A clinical photograph showing a skin lesion in context; a female subject approximately 85 years of age or older: 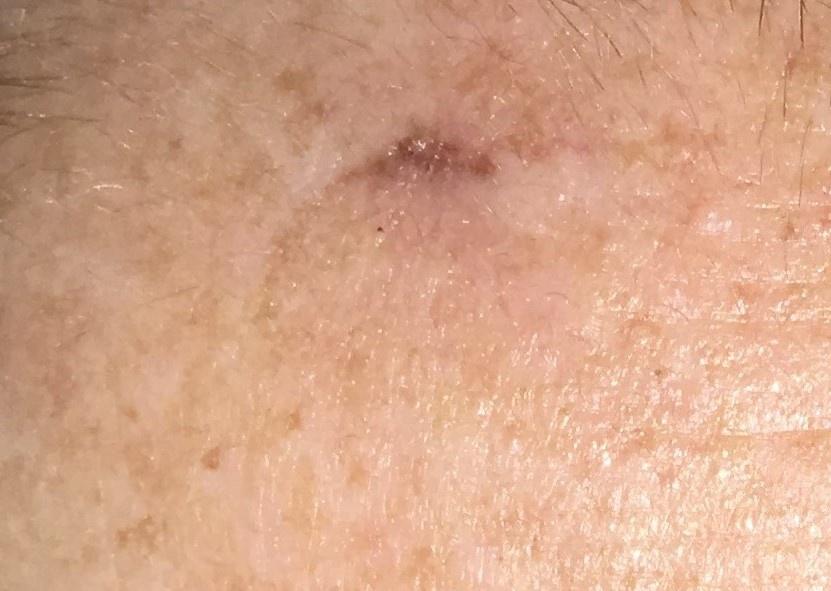Diagnosis:
Histopathologically confirmed as a basal cell carcinoma.